The lesion is described as rough or flaky. Female patient, age 18–29. The photo was captured at an angle. The patient reports the condition has been present for less than one week. Self-categorized by the patient as a rash. Located on the head or neck — 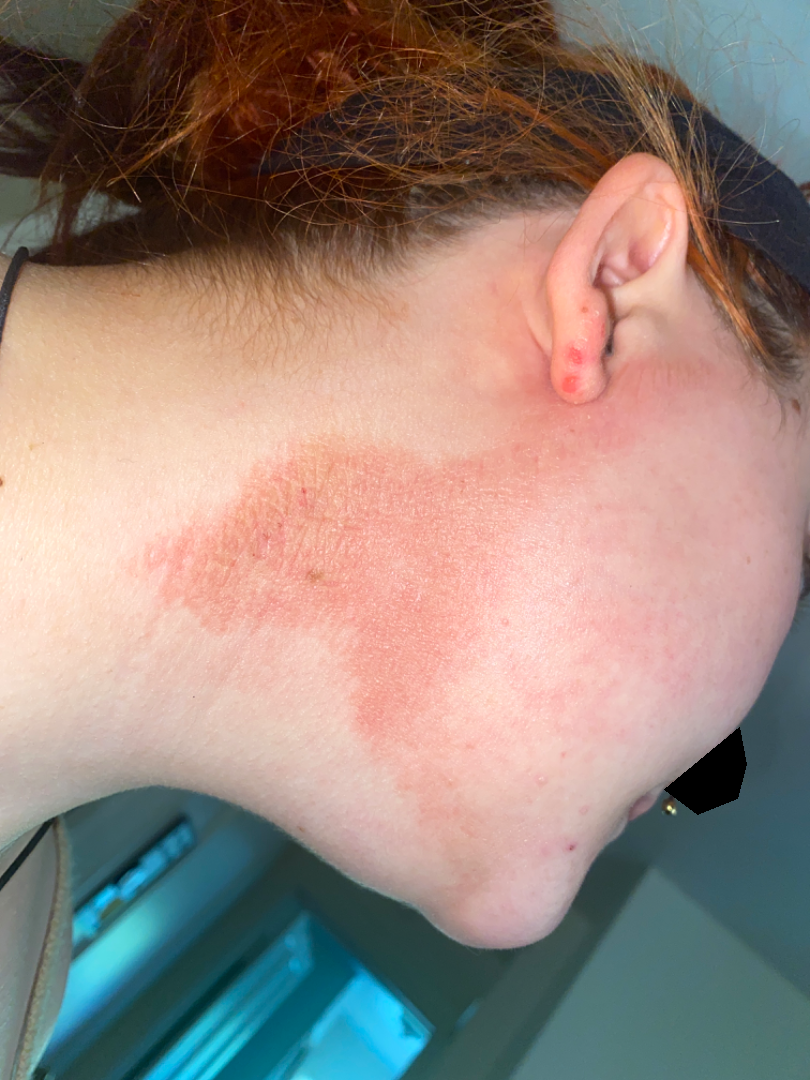<dermatology_case>
<differential>
  <tied_lead>Allergic Contact Dermatitis, Irritant Contact Dermatitis</tied_lead>
</differential>
</dermatology_case>